The contributor is 18–29, female; the affected area is the arm; a close-up photograph: 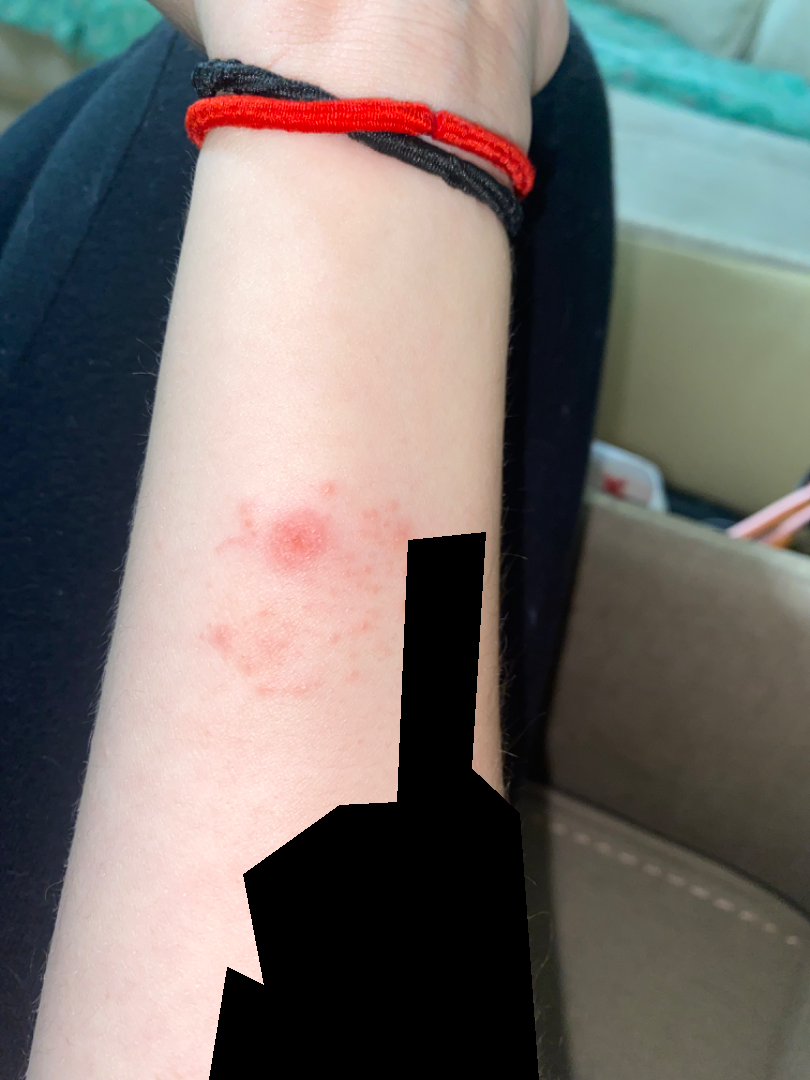assessment: indeterminate from the photograph.